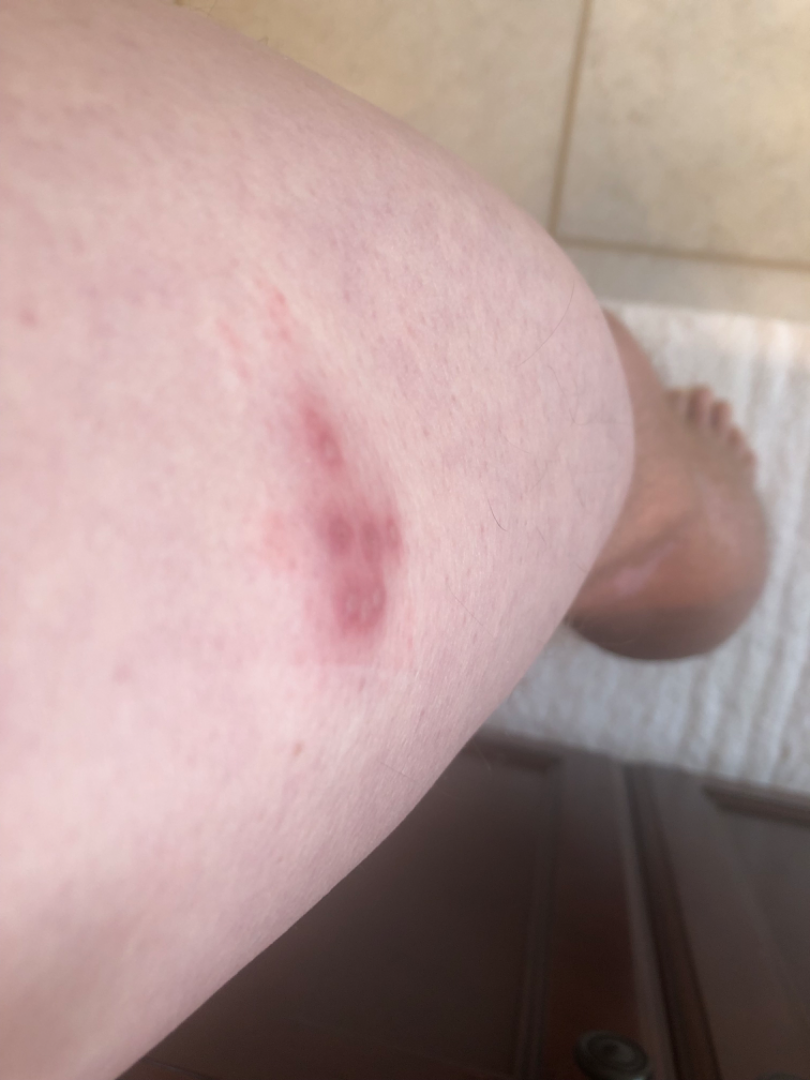texture=raised or bumpy and fluid-filled | shot type=at an angle | body site=leg | skin tone=Fitzpatrick skin type II; lay graders estimated Monk skin tone scale 1 (US pool) or 2 (India pool) | assessment=the leading consideration is Herpes Simplex; the differential also includes Herpes Zoster.